A female subject roughly 60 years of age · a skin lesion imaged with a dermatoscope: 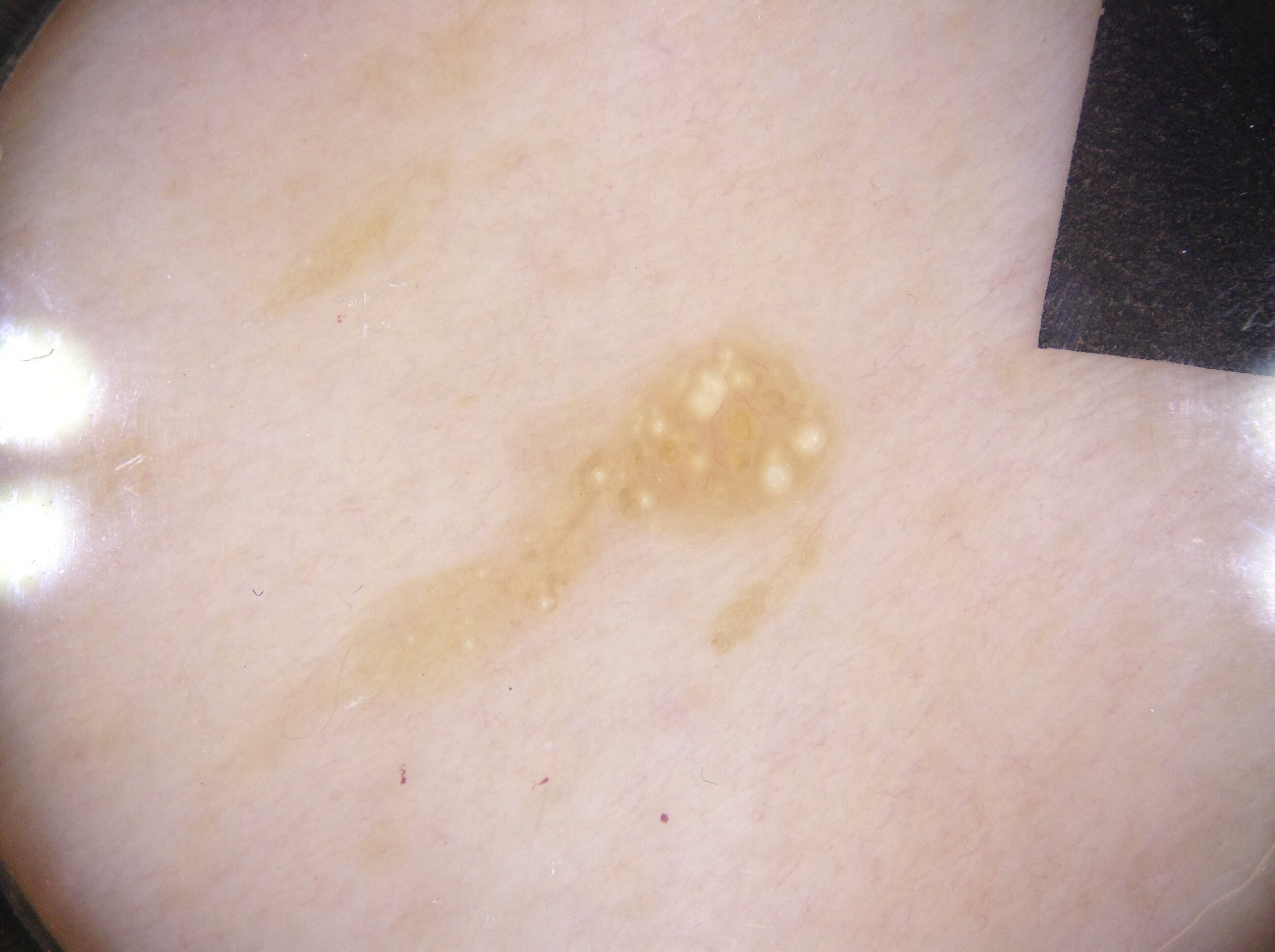Q: Which dermoscopic features were noted?
A: milia-like cysts; absent: negative network, pigment network, and streaks
Q: Where is the lesion located?
A: [280,324,852,736]
Q: What did the assessment conclude?
A: a seborrheic keratosis, a benign skin lesion